A smartphone photograph of a skin lesion. A subject aged 51: 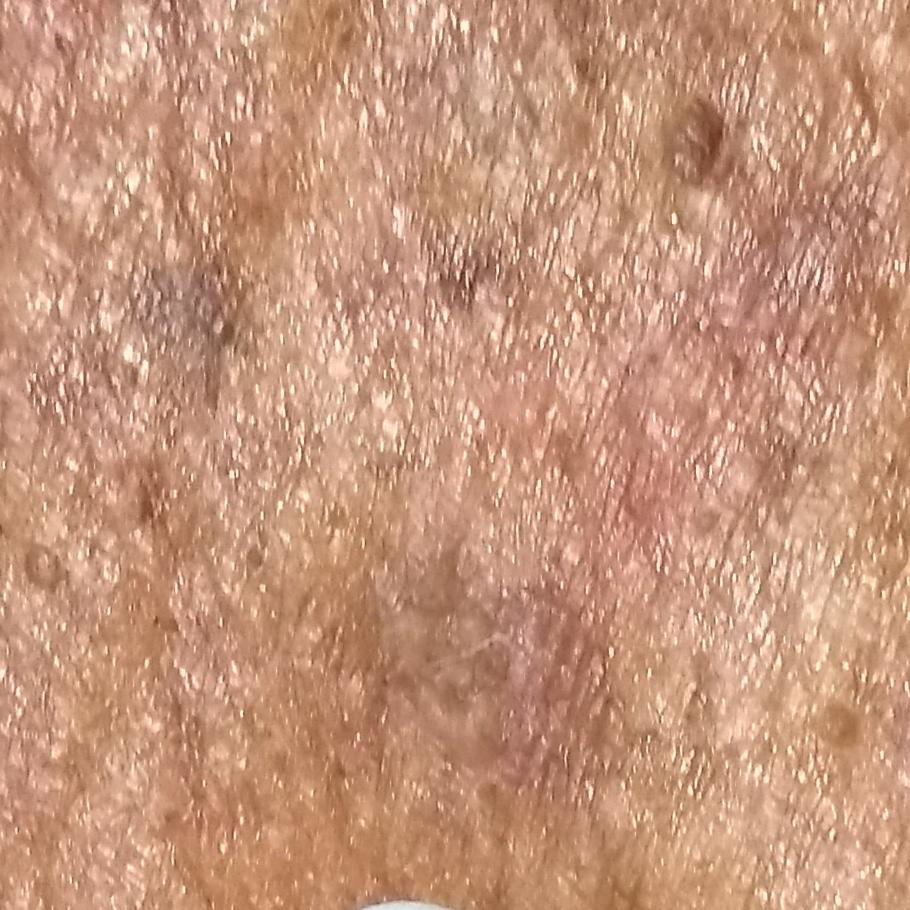Clinical context:
The lesion is located on an arm. By the patient's account, the lesion itches.
Impression:
Consistent with an actinic keratosis.